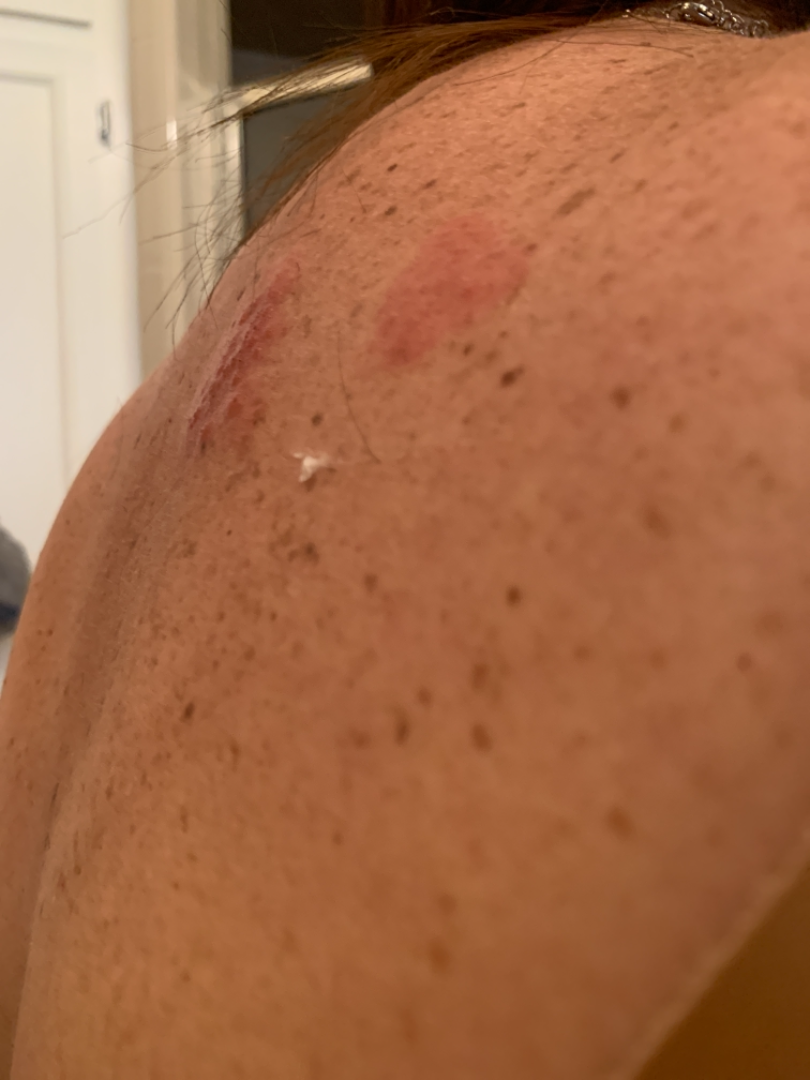| key | value |
|---|---|
| location | back of the torso |
| view | at an angle |
| patient | female |
| clinical impression | three dermatologists independently reviewed the case: most likely Herpes Zoster; an alternative is Contact dermatitis; less probable is Allergic Contact Dermatitis |